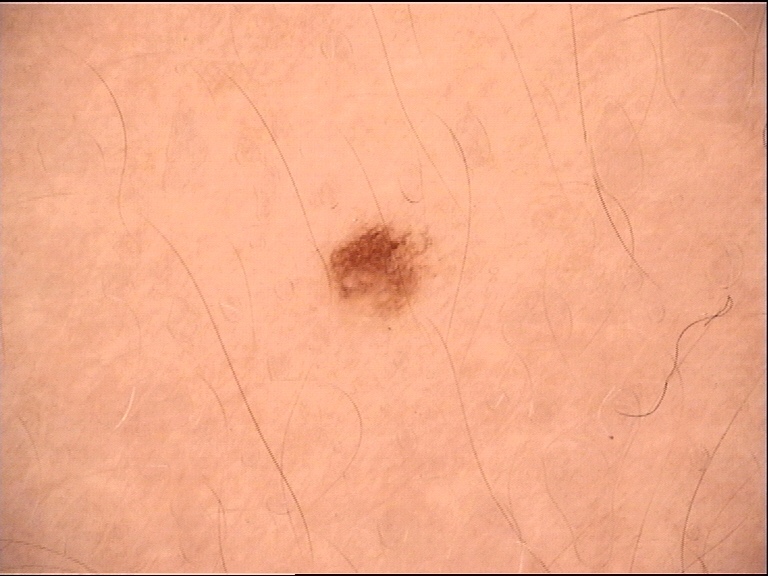Dermoscopy of a skin lesion.
The diagnosis was a benign lesion — a dysplastic junctional nevus.